A male subject in their mid- to late 40s; a dermoscopic close-up of a skin lesion — 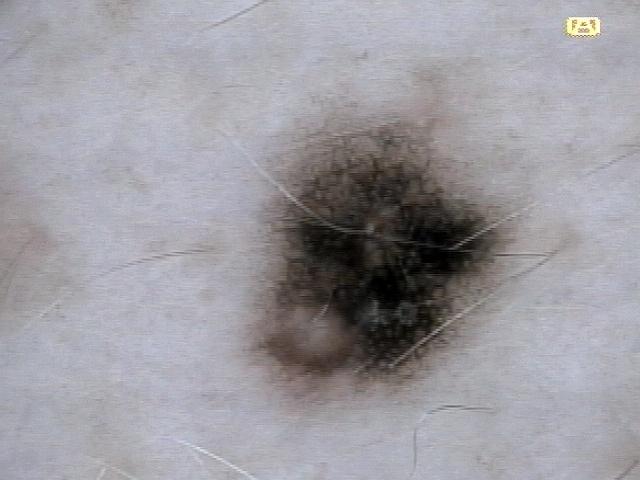Notes:
- site — the trunk
- pathology — Nevus (biopsy-proven)